A skin lesion imaged with a dermatoscope. A female subject aged around 25.
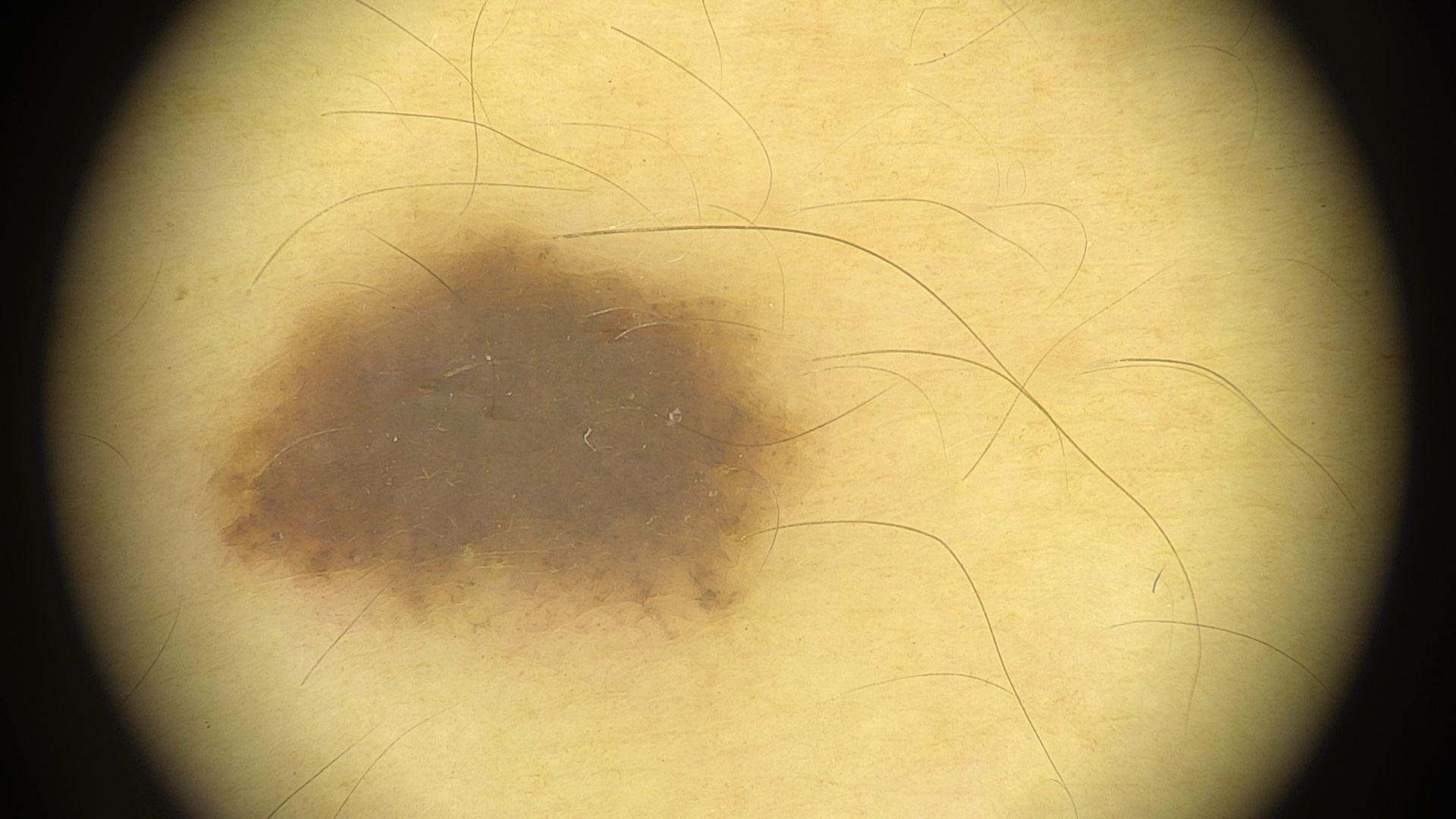Assessment: Expert review favored a nevus.